A dermoscopy image of a single skin lesion.
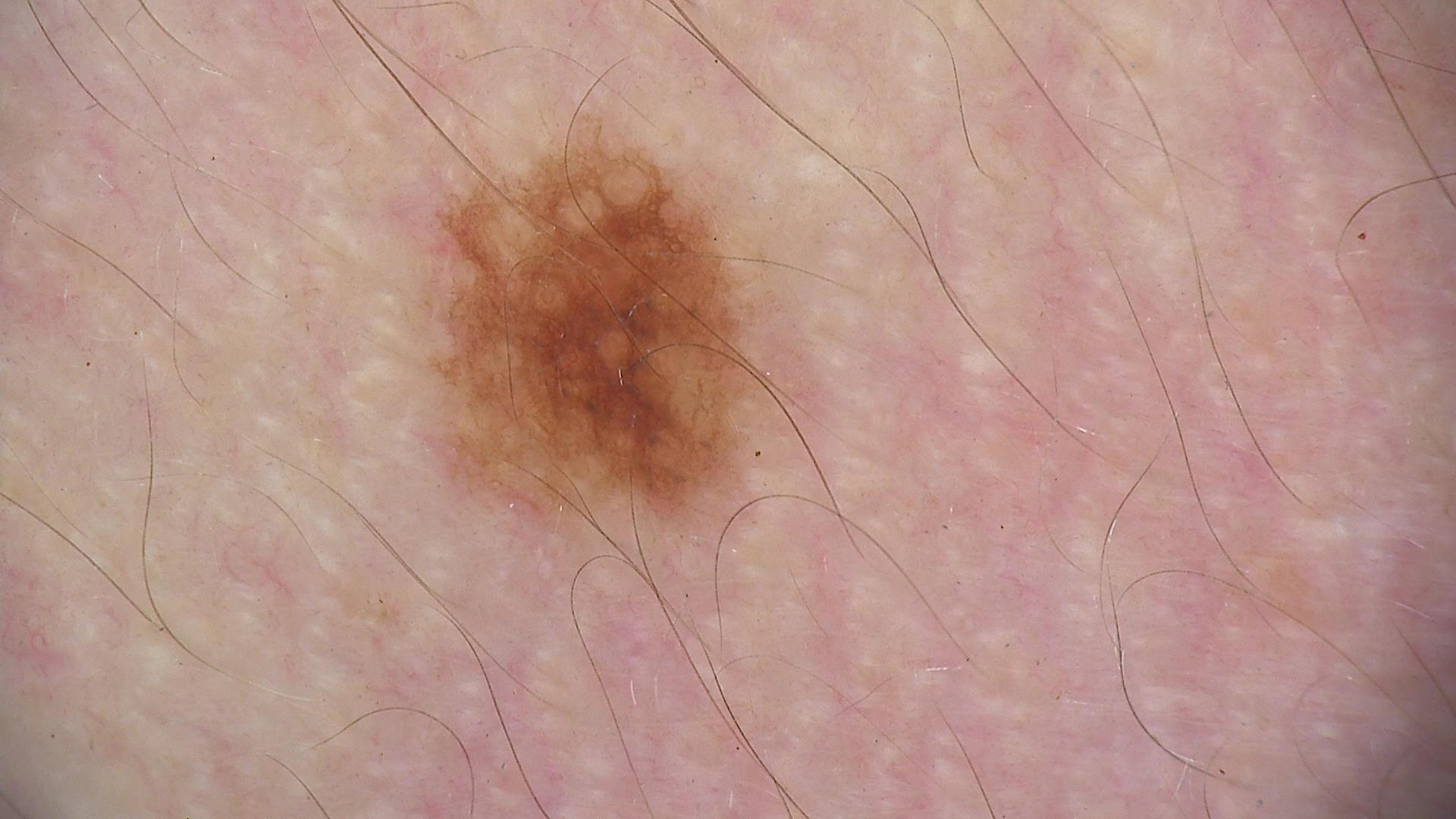Impression: Diagnosed as a banal lesion — a Miescher nevus.